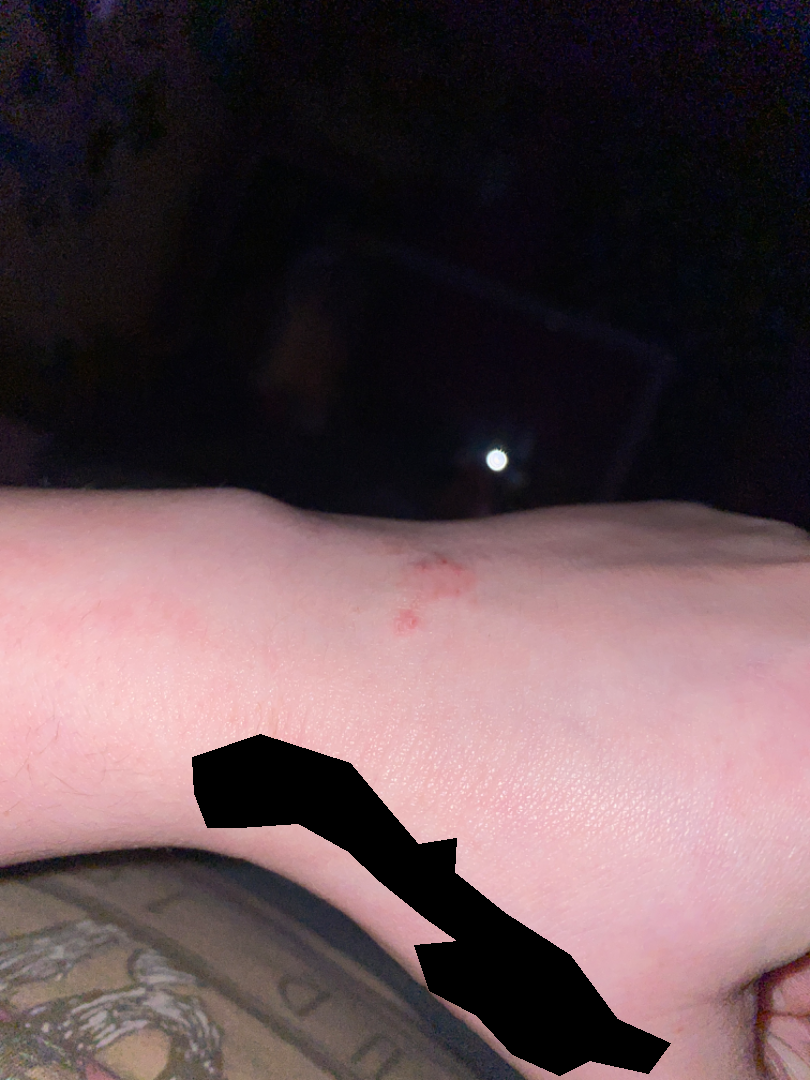Patient information: The photo was captured at an angle. The contributor is a female aged 18–29. No relevant systemic symptoms. The patient reported no relevant symptoms from the lesion. Reported duration is less than one week. Texture is reported as raised or bumpy and rough or flaky. The back of the hand is involved. Review: On photographic review by a dermatologist, Allergic Contact Dermatitis (primary); Irritant Contact Dermatitis (possible).